A skin lesion imaged with a dermatoscope:
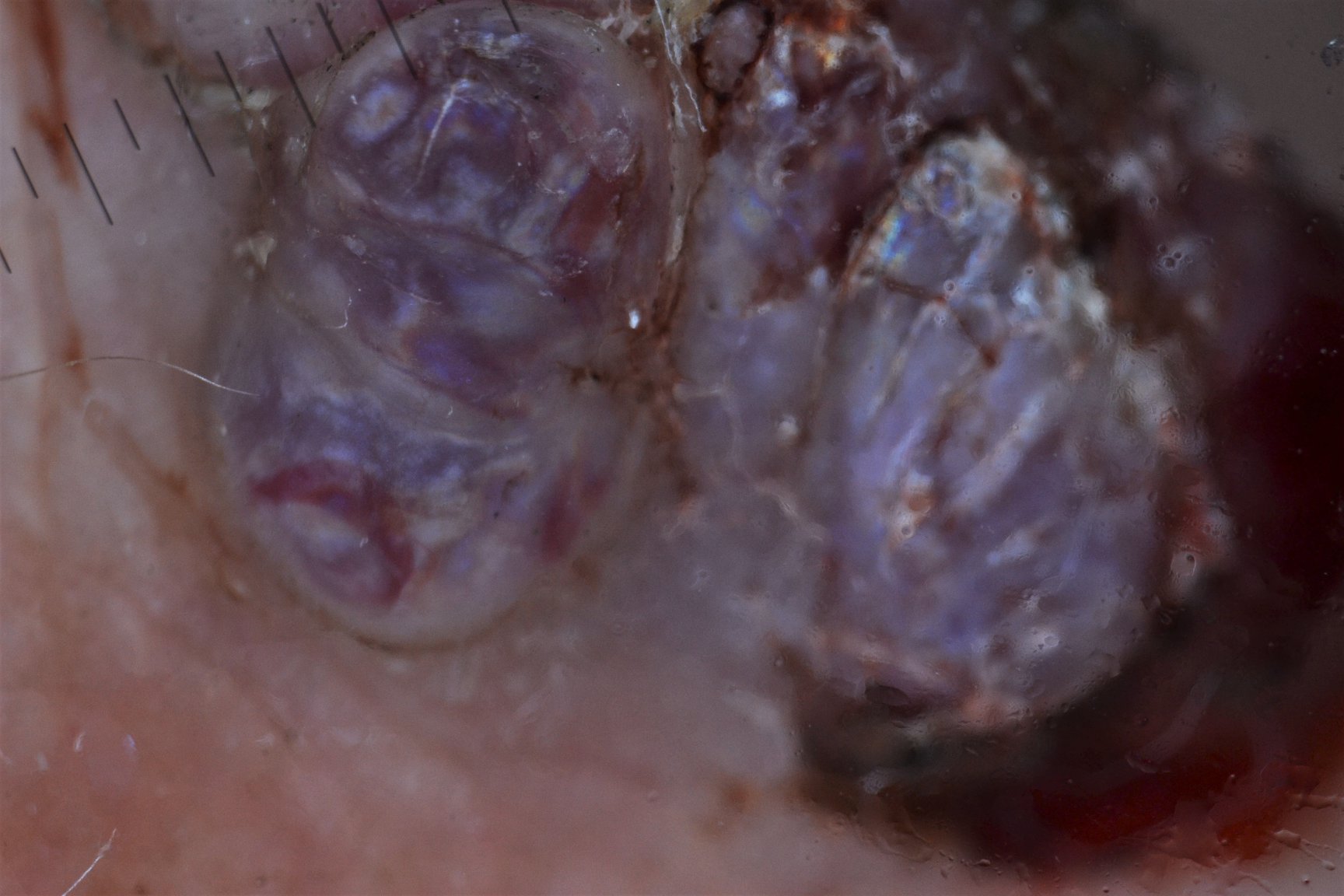Findings:
This is a vascular lesion.
Pathology:
The biopsy diagnosis was a malignancy — a Kaposi sarcoma.